The lesion is associated with itching, pain and burning; the photo was captured at a distance; the patient is 18–29, female; the patient considered this a rash; the lesion is described as raised or bumpy; the contributor notes the condition has been present for more than one year; the lesion involves the palm, top or side of the foot, arm, back of the hand and sole of the foot — 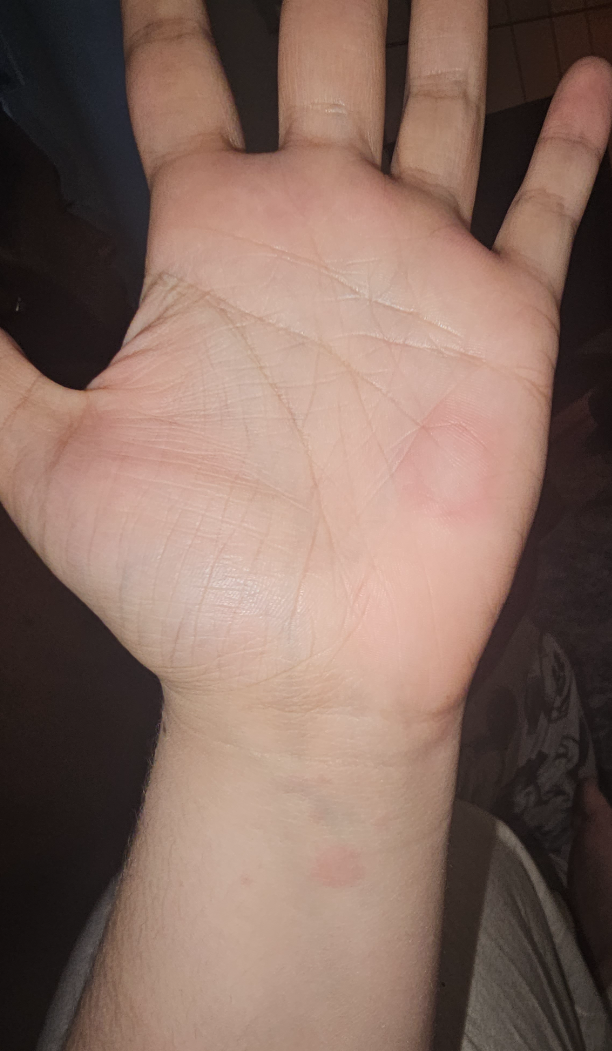differential = Drug Rash, Urticaria and Erythema multiforme were each considered, in no particular order